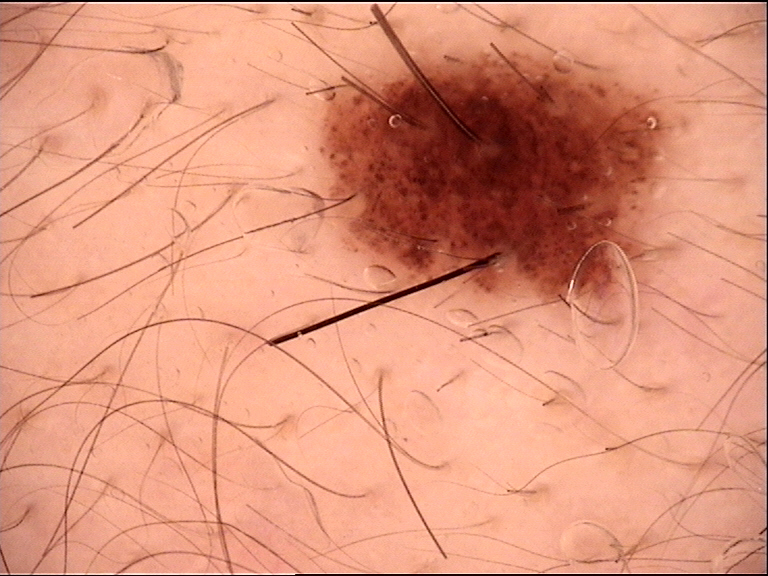Findings:
– diagnosis — compound nevus (expert consensus)